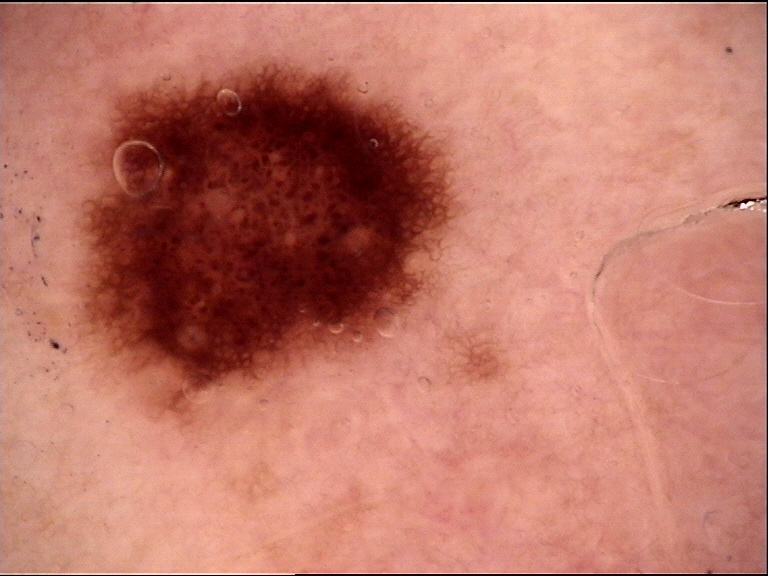Classified as a dysplastic junctional nevus.